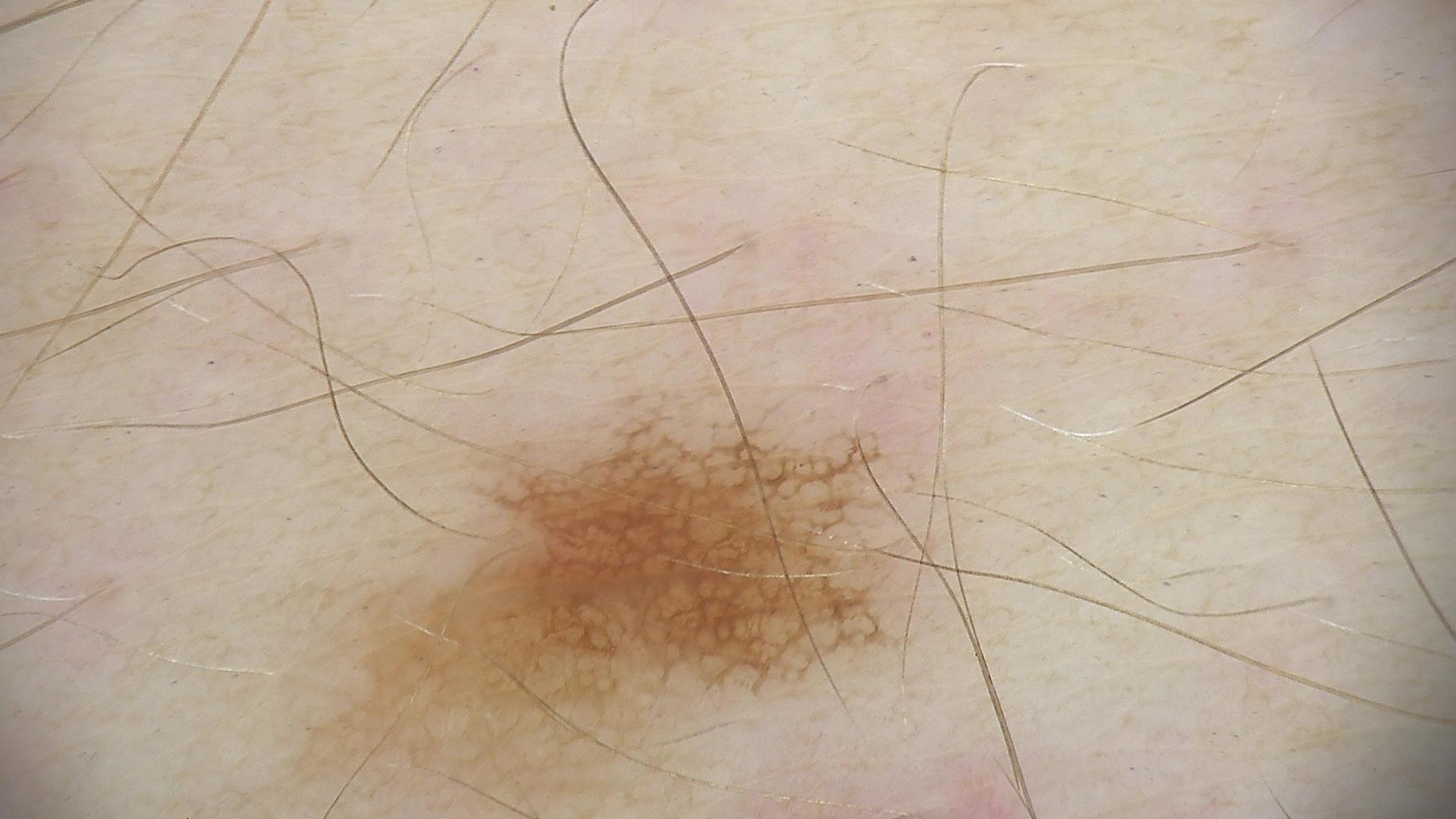Conclusion: Consistent with a dysplastic junctional nevus.